This image was taken at a distance. No relevant systemic symptoms. The subject is a female aged 18–29. The affected area is the back of the hand. Symptoms reported: itching. The patient considered this a rash. The condition has been present for less than one week: 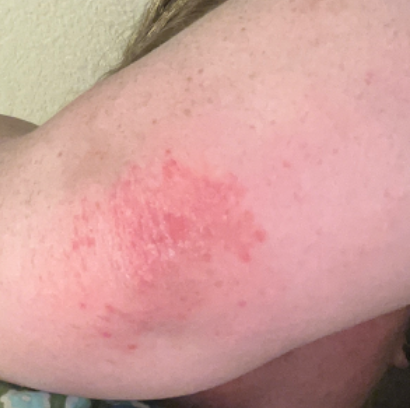<case>
  <differential>Psoriasis</differential>
</case>